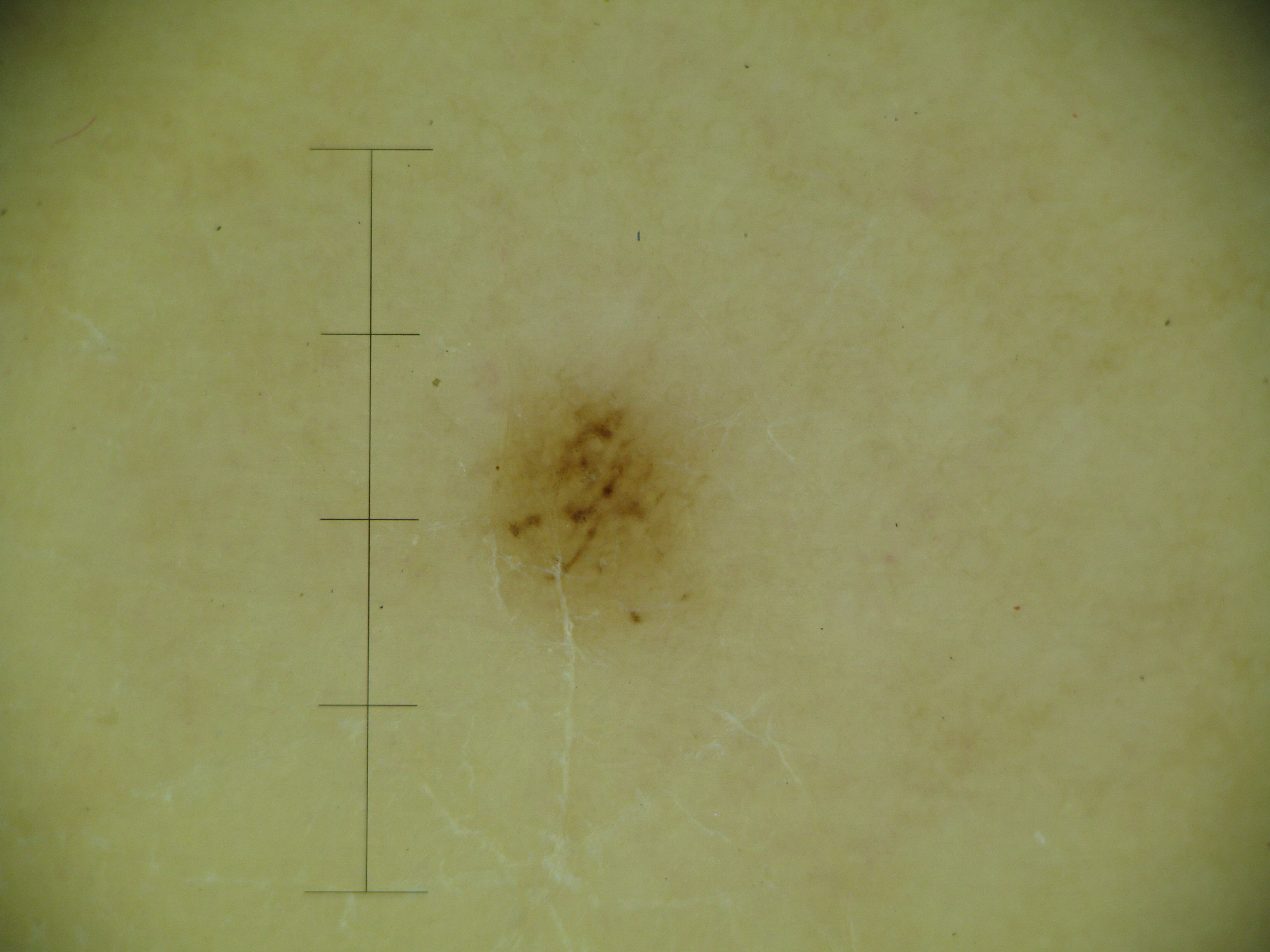The diagnostic label was an acral dysplastic junctional nevus.